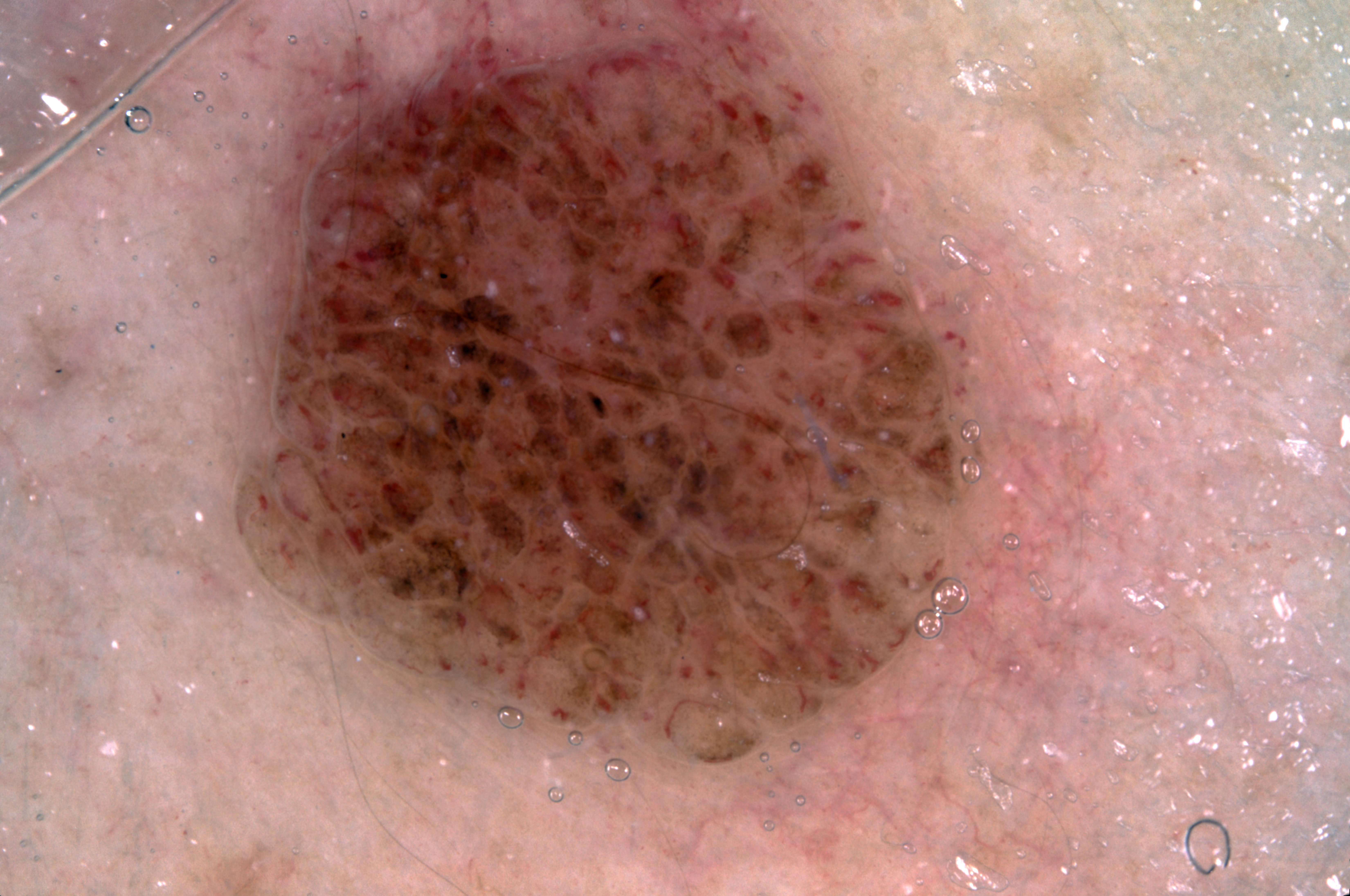<case>
<image>
  <modality>dermoscopy</modality>
</image>
<patient>
  <sex>female</sex>
  <age_approx>30</age_approx>
</patient>
<lesion_location>
  <bbox_xyxy>229, 0, 1017, 773</bbox_xyxy>
</lesion_location>
<dermoscopic_features>
  <present/>
  <absent>streaks, pigment network, negative network, milia-like cysts</absent>
</dermoscopic_features>
<diagnosis>
  <name>melanocytic nevus</name>
  <malignancy>benign</malignancy>
  <lineage>melanocytic</lineage>
  <provenance>clinical</provenance>
</diagnosis>
</case>